The lesion involves the leg. A close-up photograph. Male subject, age 60–69:
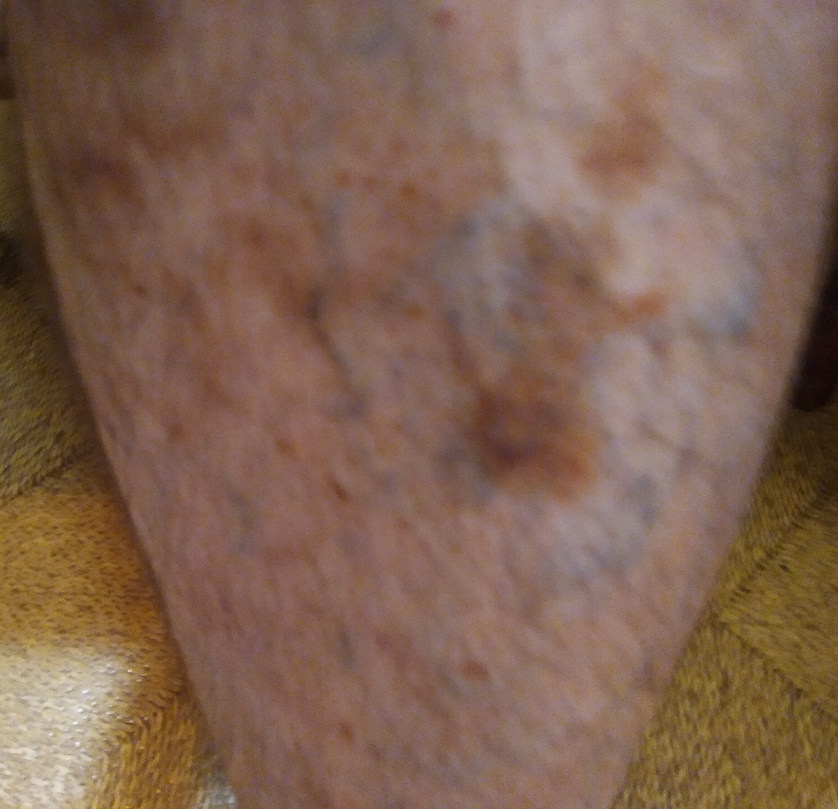The lesion is described as flat. The condition has been present for more than one year. Self-categorized by the patient as a growth or mole. On photographic review, in keeping with Pigmented purpuric eruption.